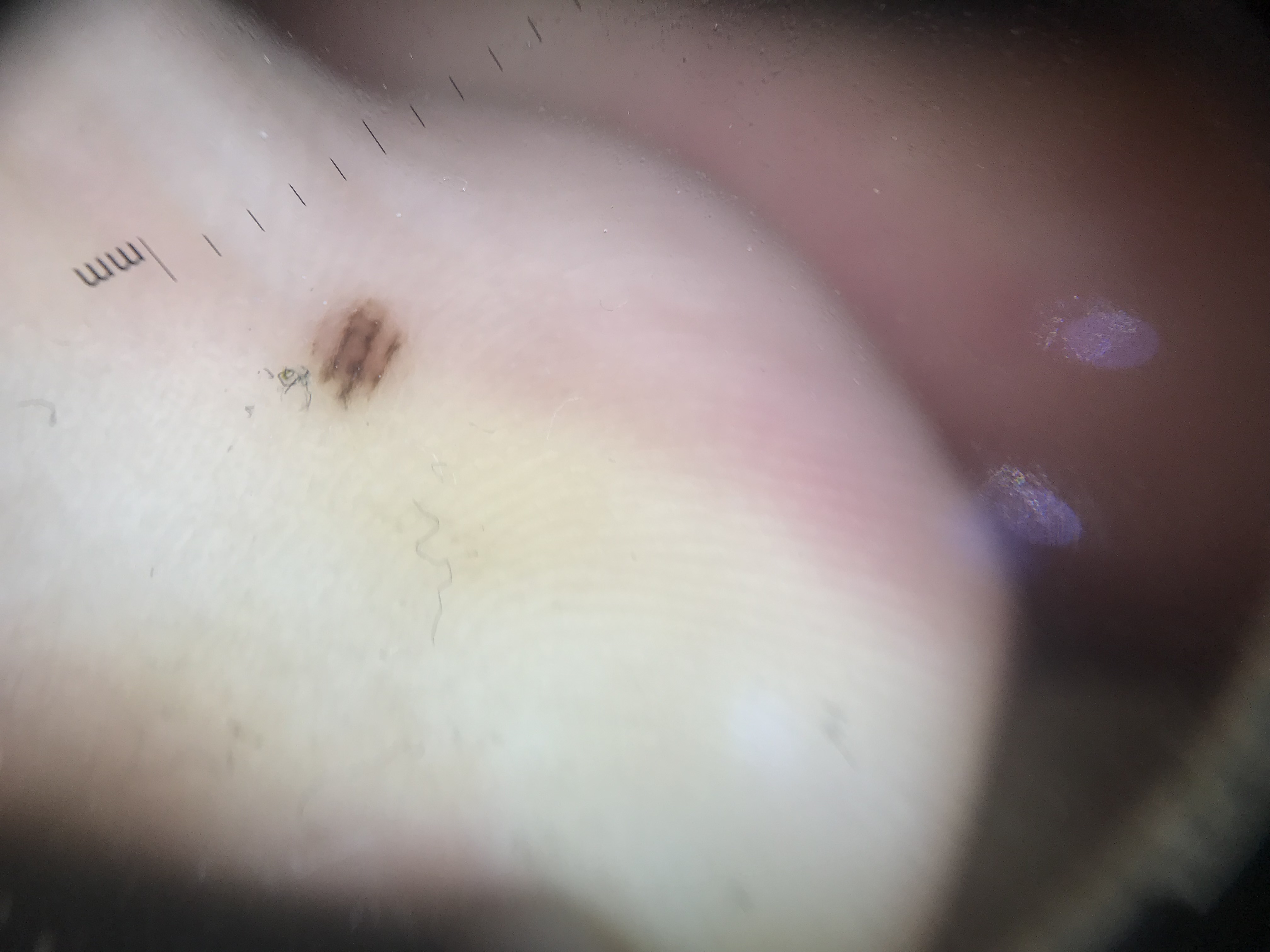| field | value |
|---|---|
| diagnostic label | acral dysplastic junctional nevus (expert consensus) |